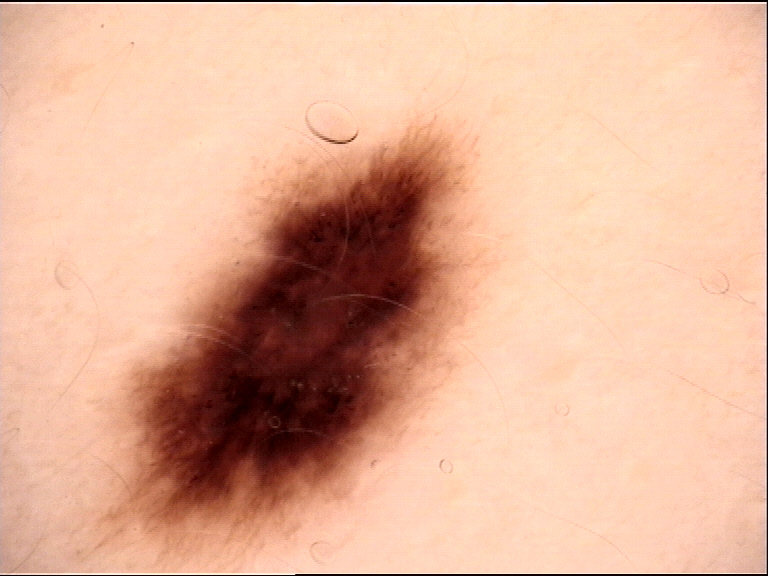Case:
* class · dysplastic junctional nevus (expert consensus)